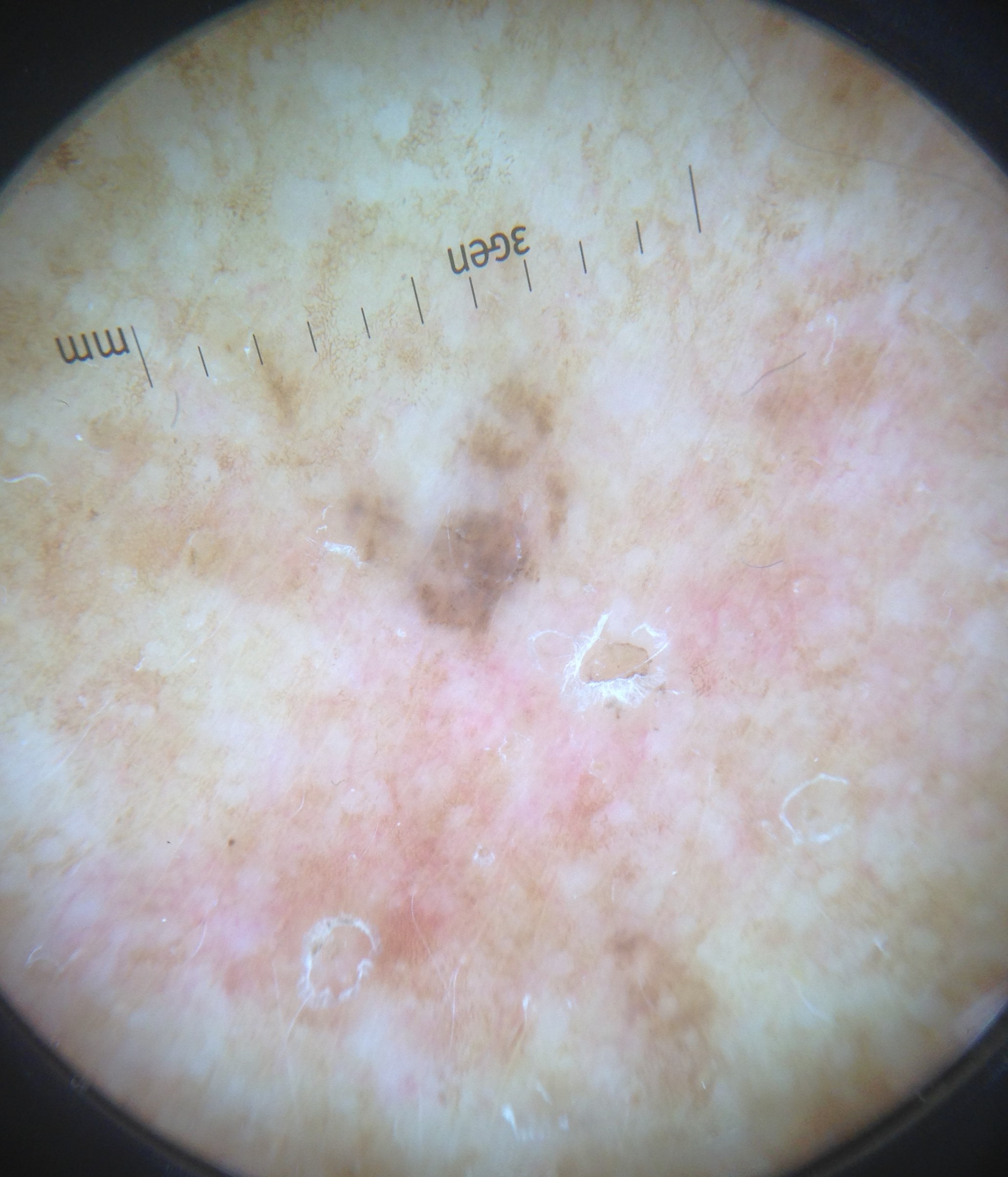Q: What is the diagnosis?
A: actinic keratosis (expert consensus)